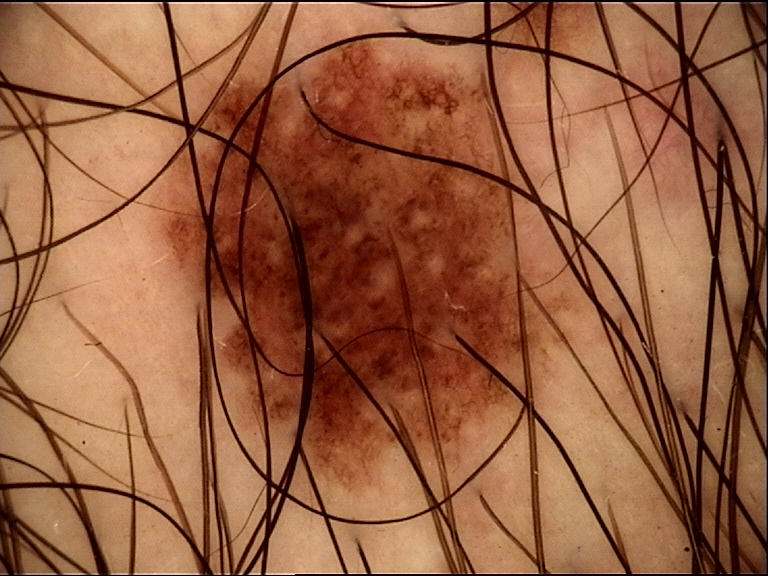  diagnosis:
    name: dysplastic junctional nevus
    code: jd
    malignancy: benign
    super_class: melanocytic
    confirmation: expert consensus